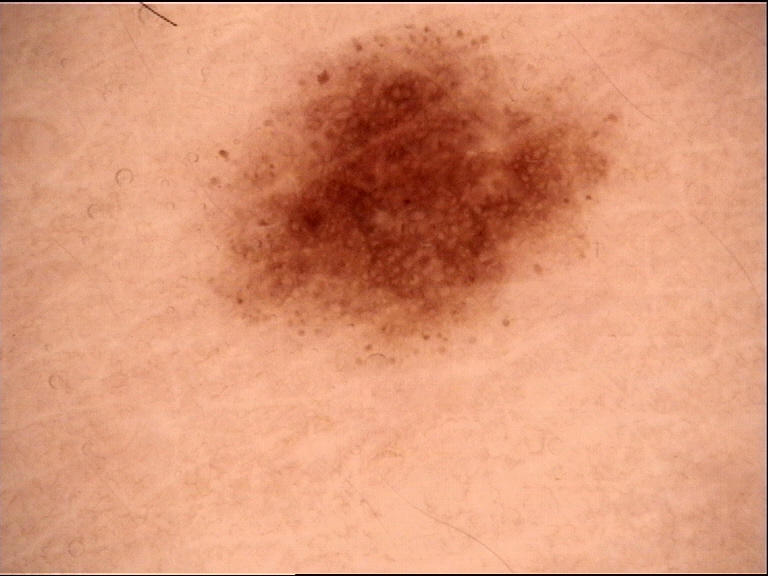Findings: Dermoscopy of a skin lesion. Impression: The diagnostic label was a dysplastic junctional nevus.